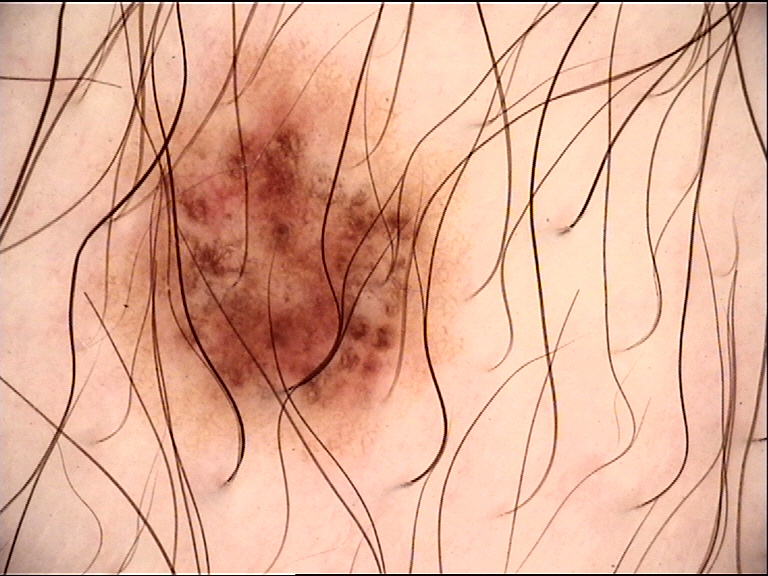A dermoscopic photograph of a skin lesion. Classified as a dysplastic junctional nevus.